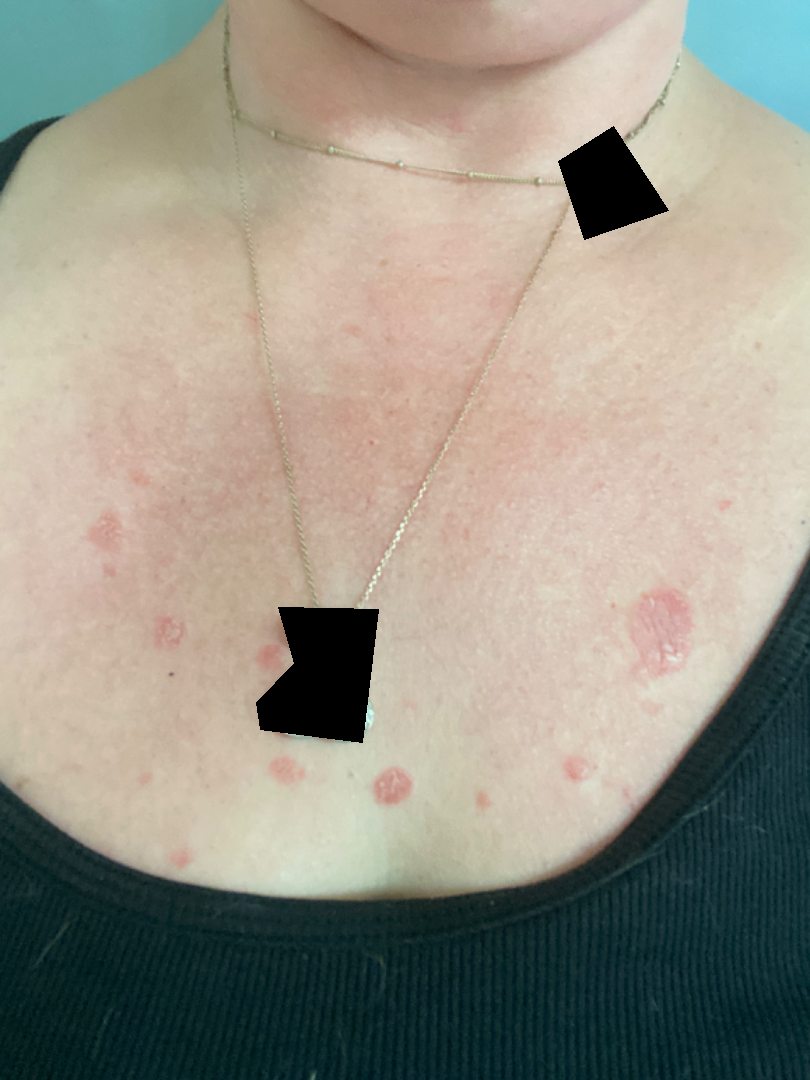Q: What is the differential diagnosis?
A: Rosacea, Allergic Contact Dermatitis and Systemic lupus erythematosus-related syndrome were considered with similar weight